A clinical photograph of a skin lesion; the patient was assessed as FST III; the chart records prior skin cancer (patient or family) and pesticide exposure; a female subject age 22: 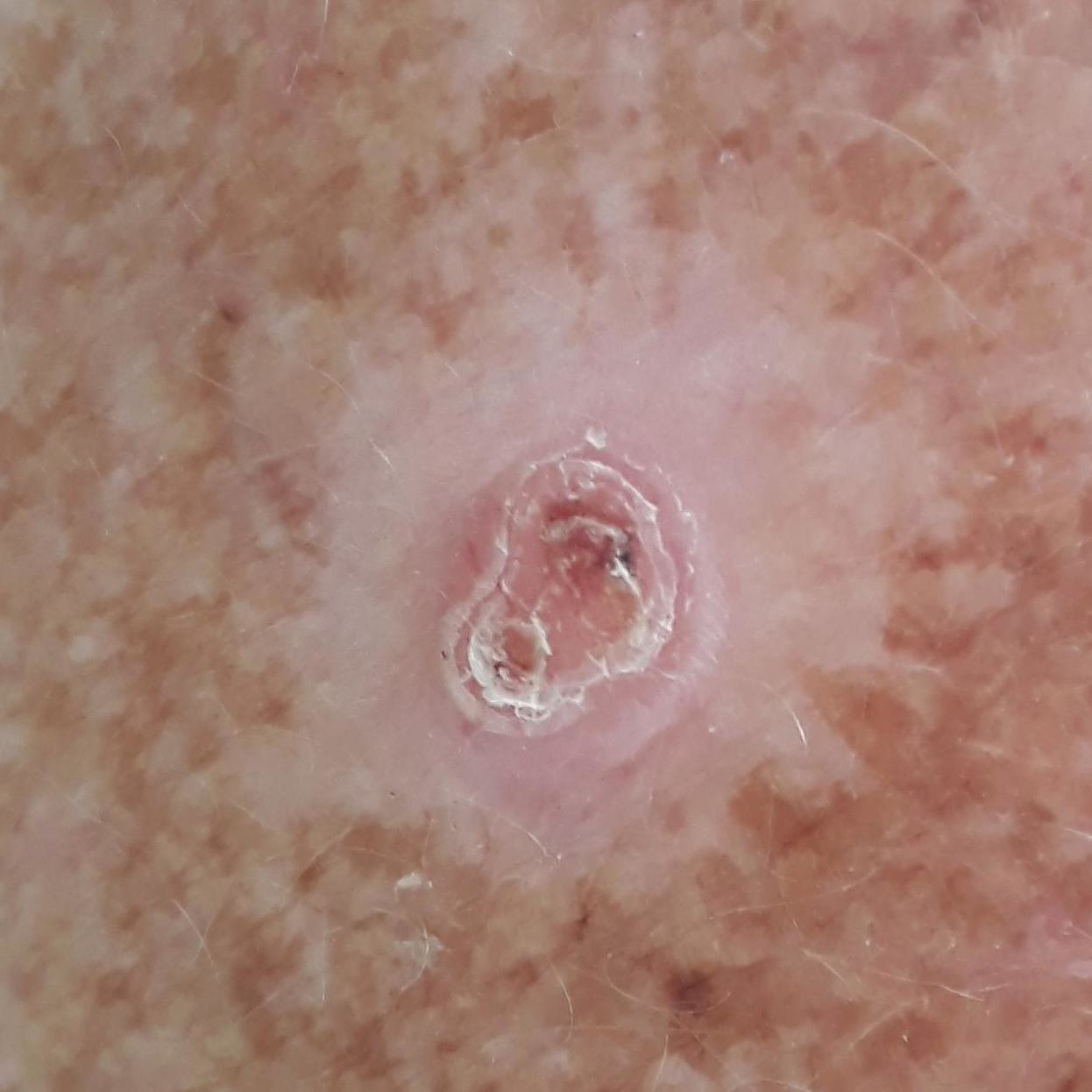Clinical context:
The lesion involves the chest. Measuring about 6 × 3 mm.
Pathology:
On biopsy, the diagnosis was a basal cell carcinoma.